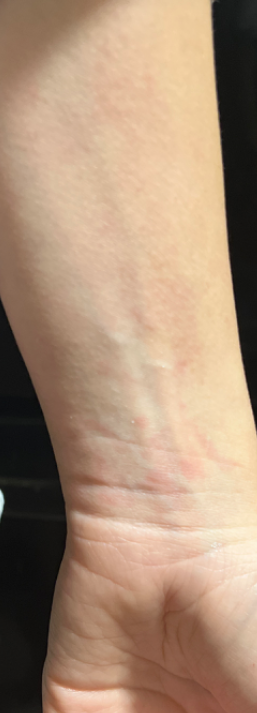Skin tone: Fitzpatrick phototype I. Texture is reported as flat. This image was taken at a distance. The lesion involves the head or neck and arm. Insect Bite (possible); Irritant Contact Dermatitis (possible); Allergic Contact Dermatitis (possible).